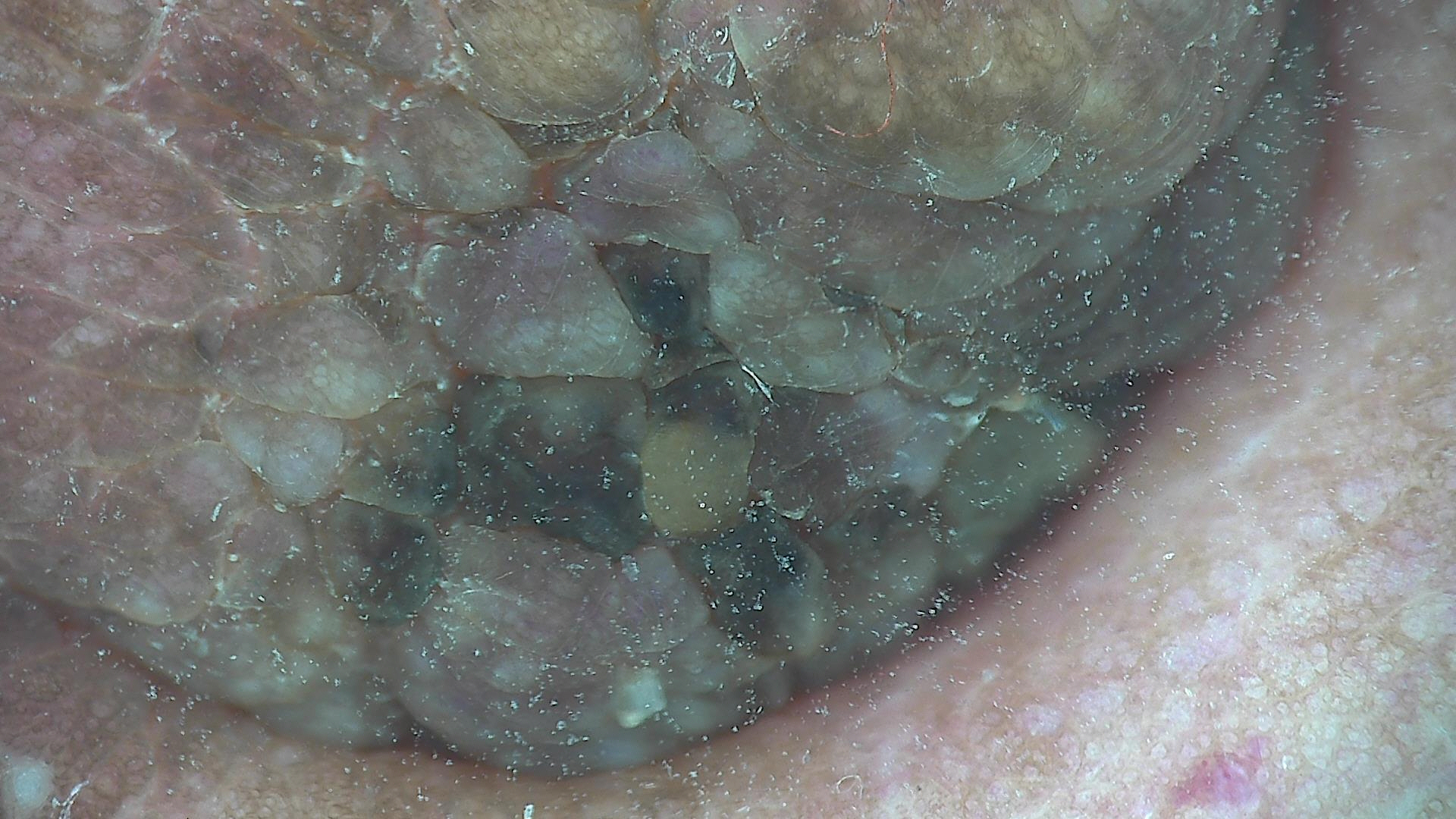classification — banal
diagnosis — dermal nevus (expert consensus)